Located on the arm; this image was taken at an angle — 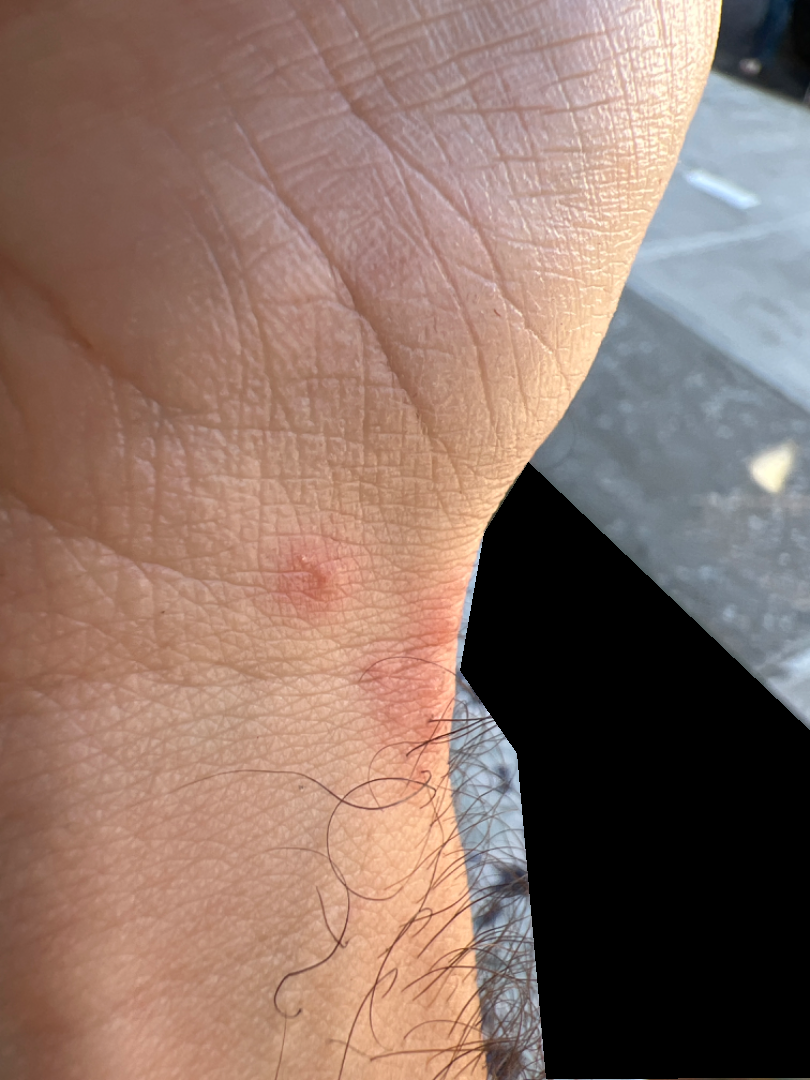Q: Fitzpatrick or Monk tone?
A: Fitzpatrick skin type III
Q: Texture?
A: raised or bumpy
Q: What symptoms does the patient report?
A: burning
Q: How long has this been present?
A: about one day
Q: Patient's own categorization?
A: a rash
Q: What is the differential diagnosis?
A: Insect Bite (0.56); Eczema (0.25); Allergic Contact Dermatitis (0.19)